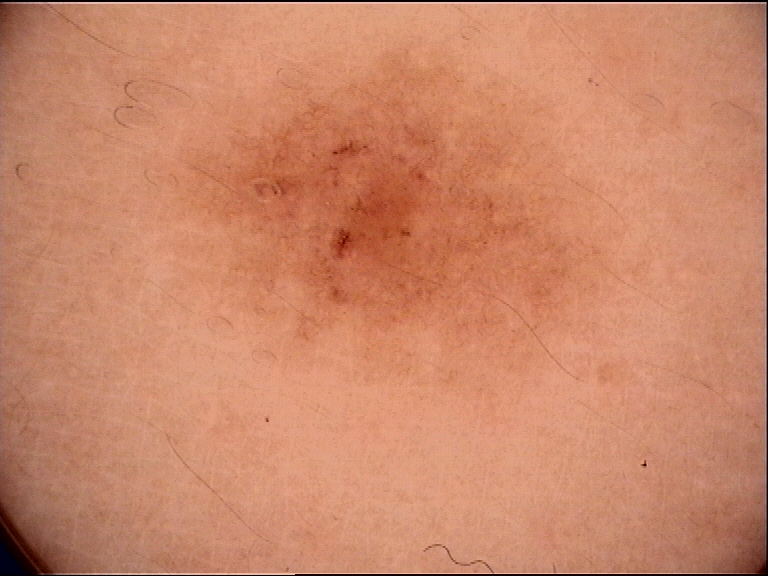Impression:
Consistent with a dysplastic junctional nevus.